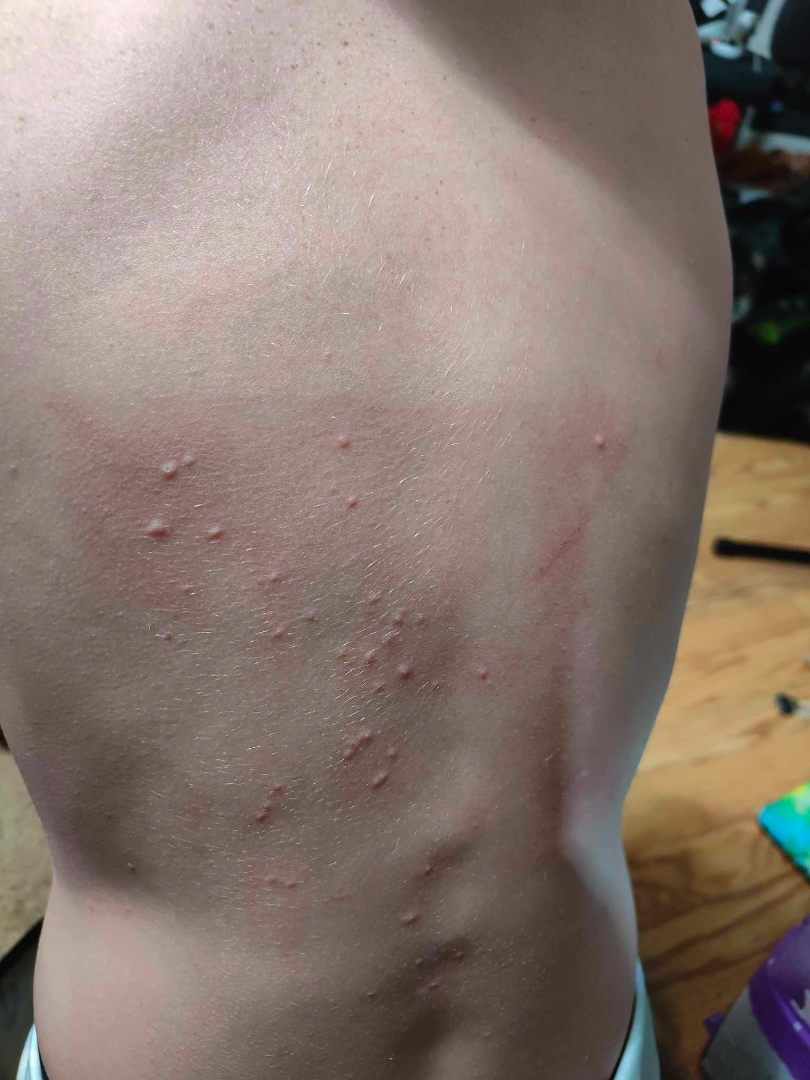assessment: most consistent with Molluscum Contagiosum; also consider Folliculitis.